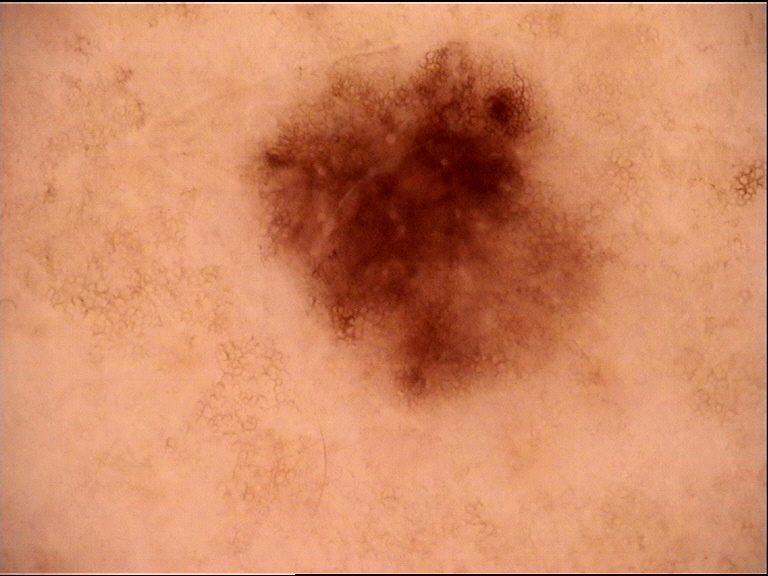Classified as a benign lesion — a dysplastic junctional nevus.